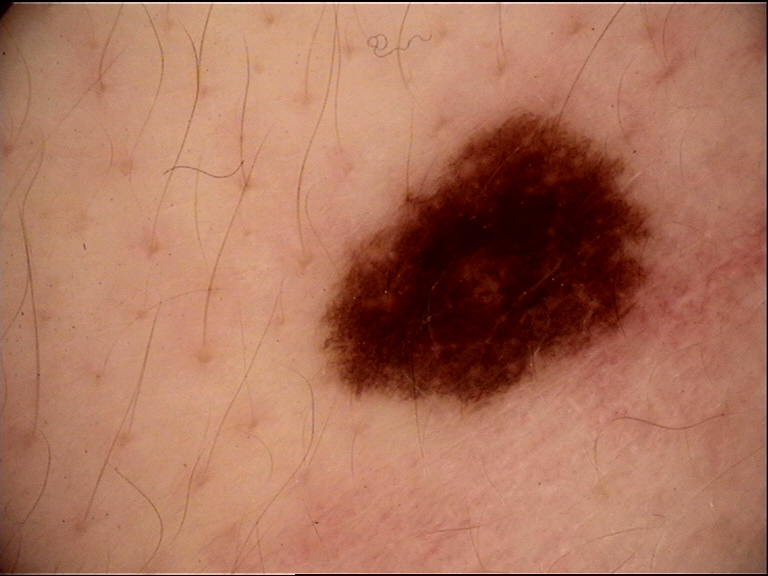Findings:
A dermoscopy image of a single skin lesion.
Impression:
Labeled as a dysplastic junctional nevus.